Reported duration is three to twelve months. The contributor notes the lesion is raised or bumpy. The top or side of the foot and sole of the foot are involved. A close-up photograph. Fitzpatrick III; non-clinician graders estimated MST 2 or 4: 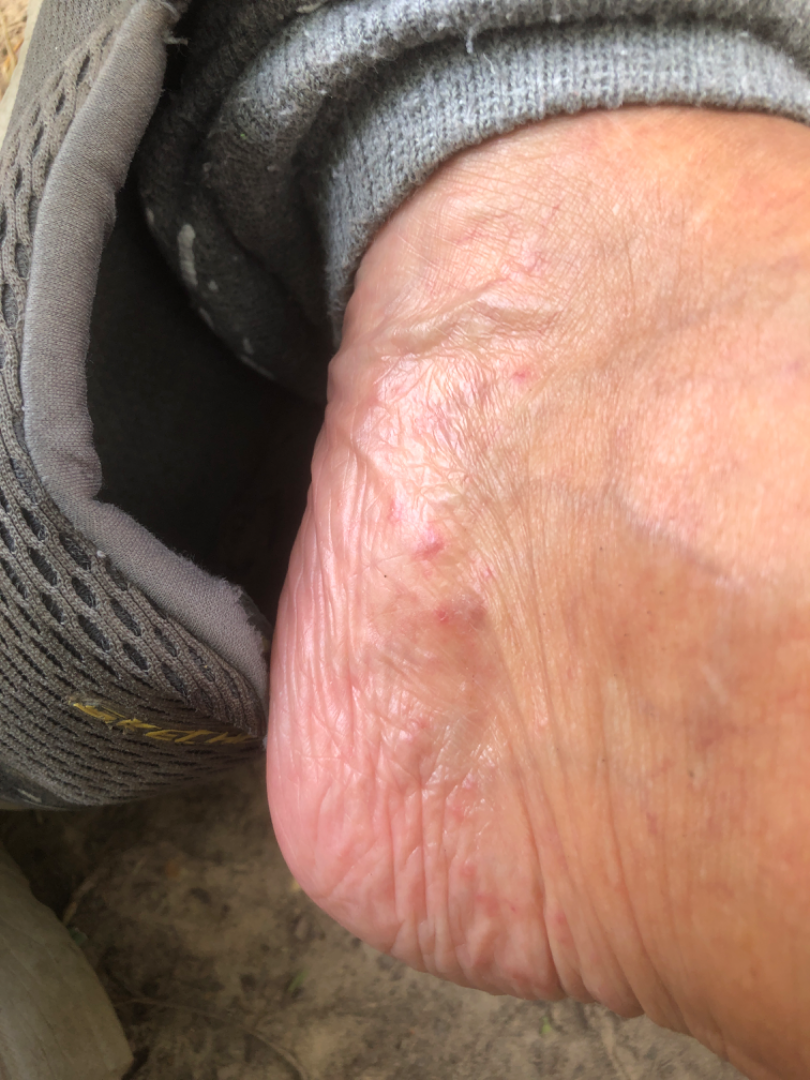differential = Tinea (leading); Eczema (possible); Psoriasis (remote).